The patient is FST II; the chart records prior malignancy (patient or family) and tobacco use; a clinical photograph showing a skin lesion; a male patient age 77.
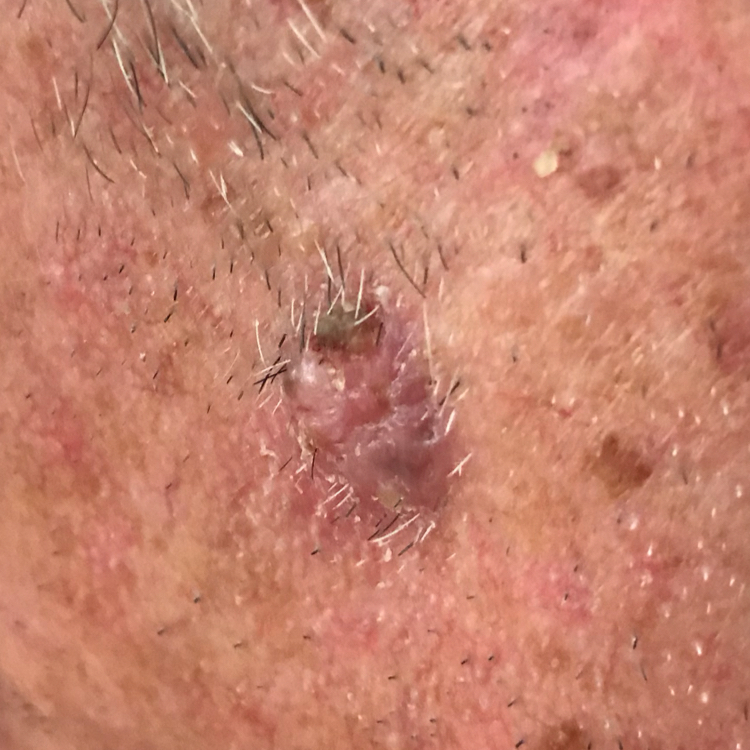<case>
  <lesion_location>the face</lesion_location>
  <lesion_size>
    <diameter_1_mm>15.0</diameter_1_mm>
    <diameter_2_mm>9.0</diameter_2_mm>
  </lesion_size>
  <diagnosis>
    <name>basal cell carcinoma</name>
    <code>BCC</code>
    <malignancy>malignant</malignancy>
    <confirmation>histopathology</confirmation>
  </diagnosis>
</case>